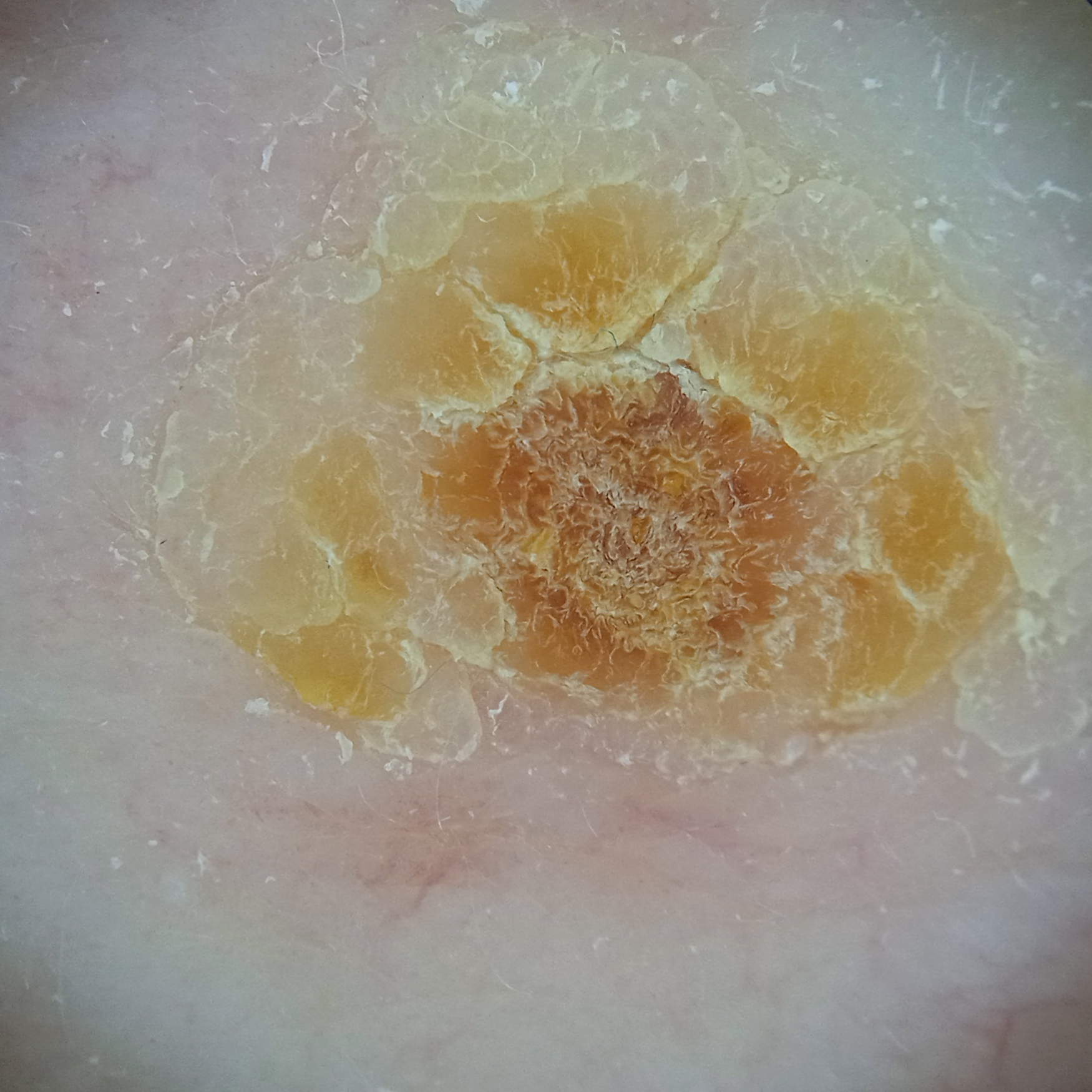– nevus count · a moderate number of melanocytic nevi
– relevant history · a personal history of skin cancer, a personal history of cancer
– patient · male, 77 years of age
– site · the back
– assessment · actinic keratosis (dermatologist consensus)